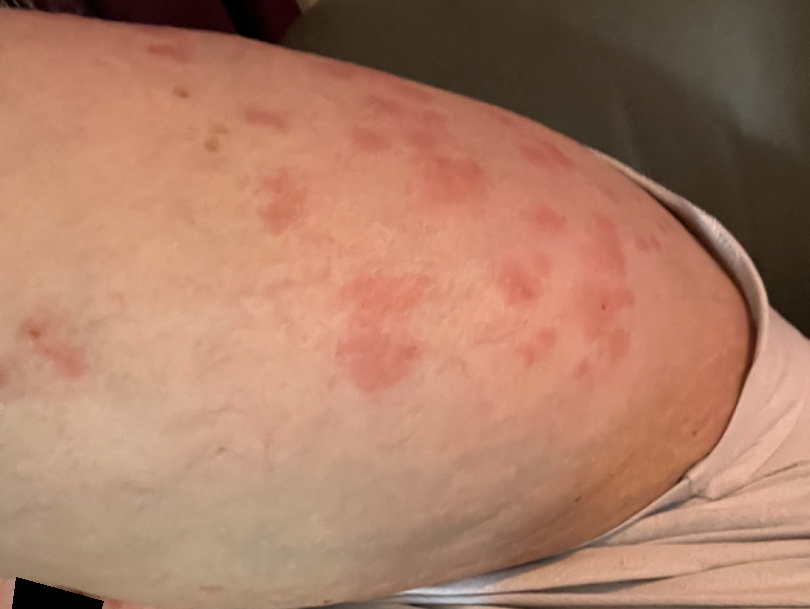{
  "assessment": "unable to determine"
}